A dermatoscopic image of a skin lesion: 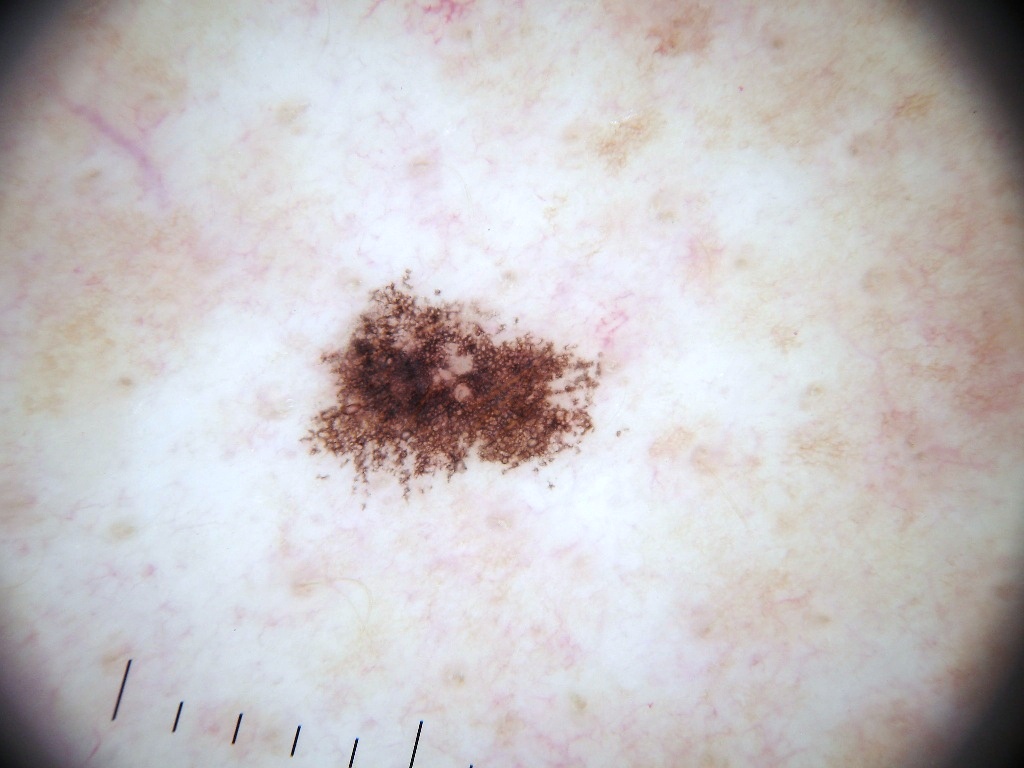The dermoscopic pattern shows neither globules nor streaks.
The lesion is small relative to the field of view.
The lesion occupies the region x1=301, y1=277, x2=623, y2=499.
The lesion was assessed as a benign lesion.